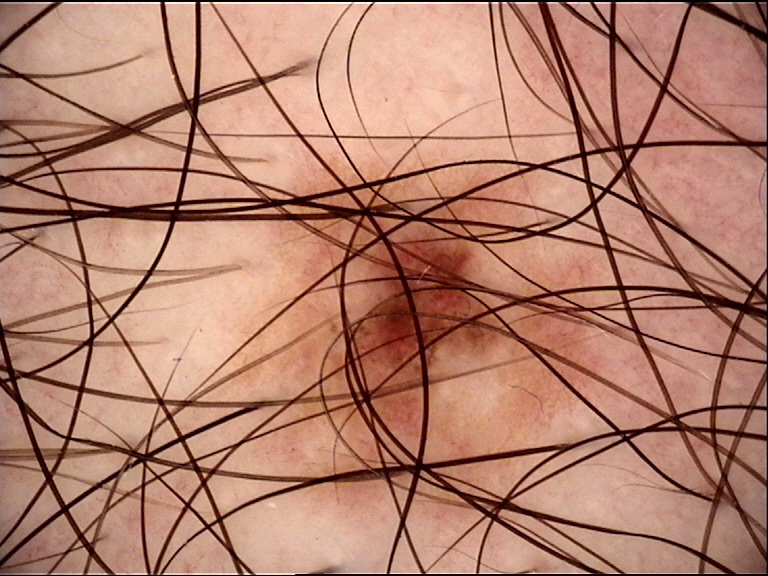Conclusion: Diagnosed as a benign lesion — a dysplastic junctional nevus.